A dermoscopy image of a single skin lesion.
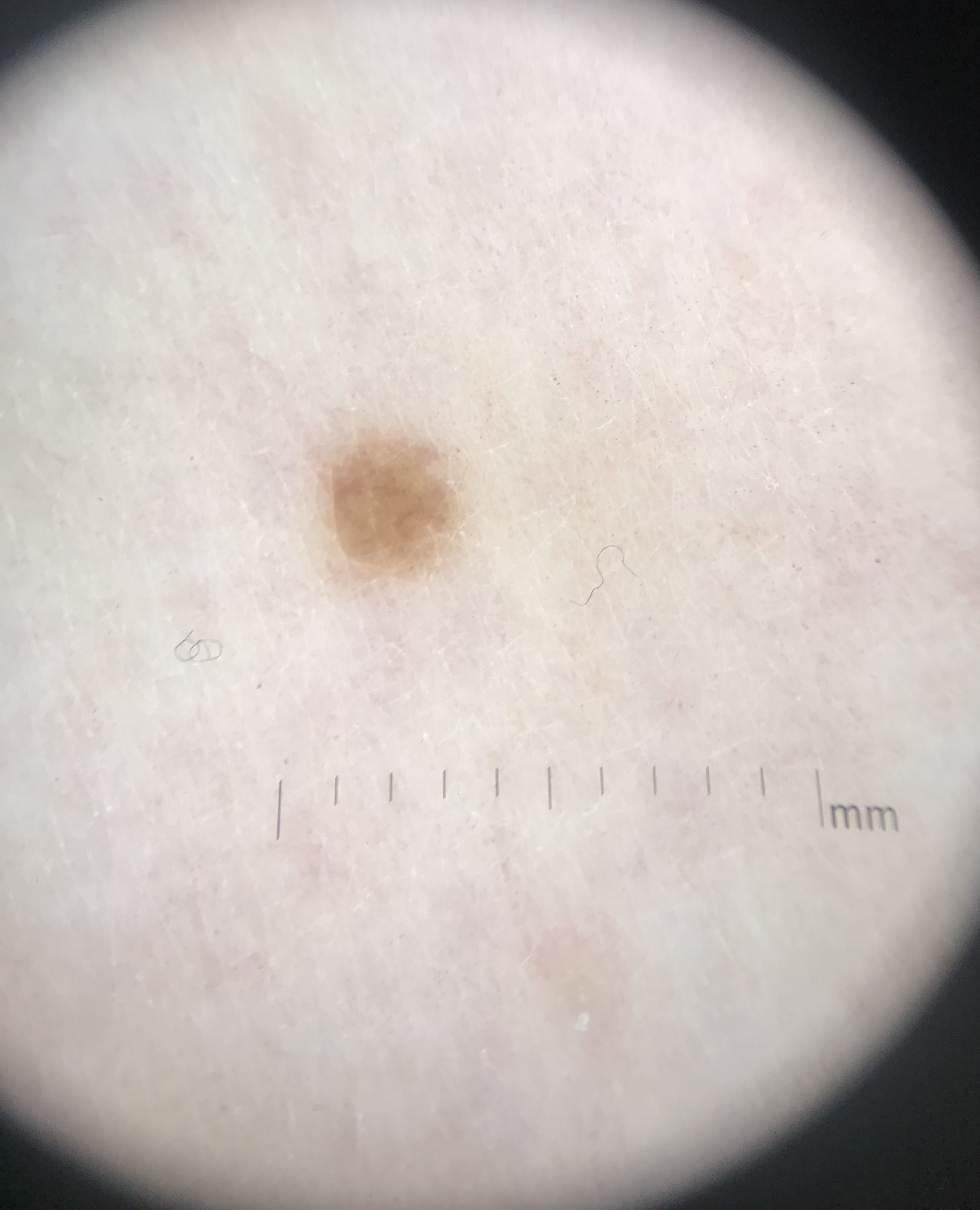Labeled as a keratinocytic, benign lesion — a seborrheic keratosis.